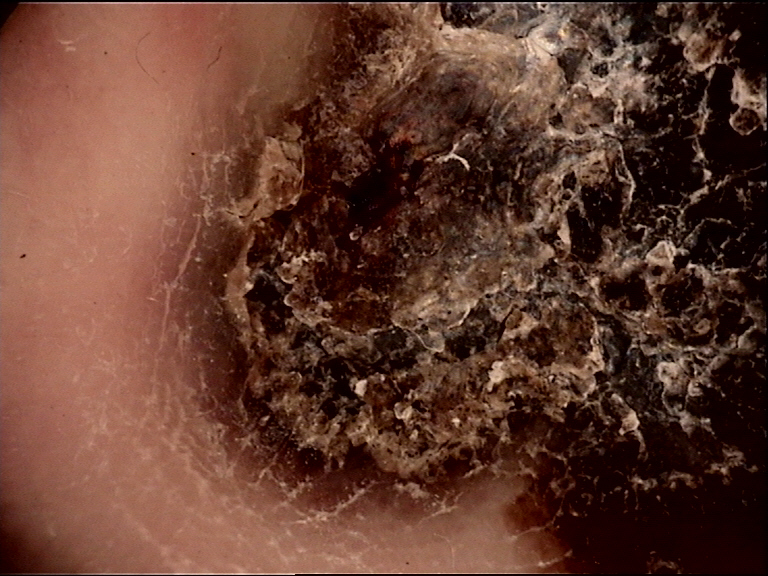pathology = acral lentiginous melanoma (biopsy-proven).